This is a close-up image: 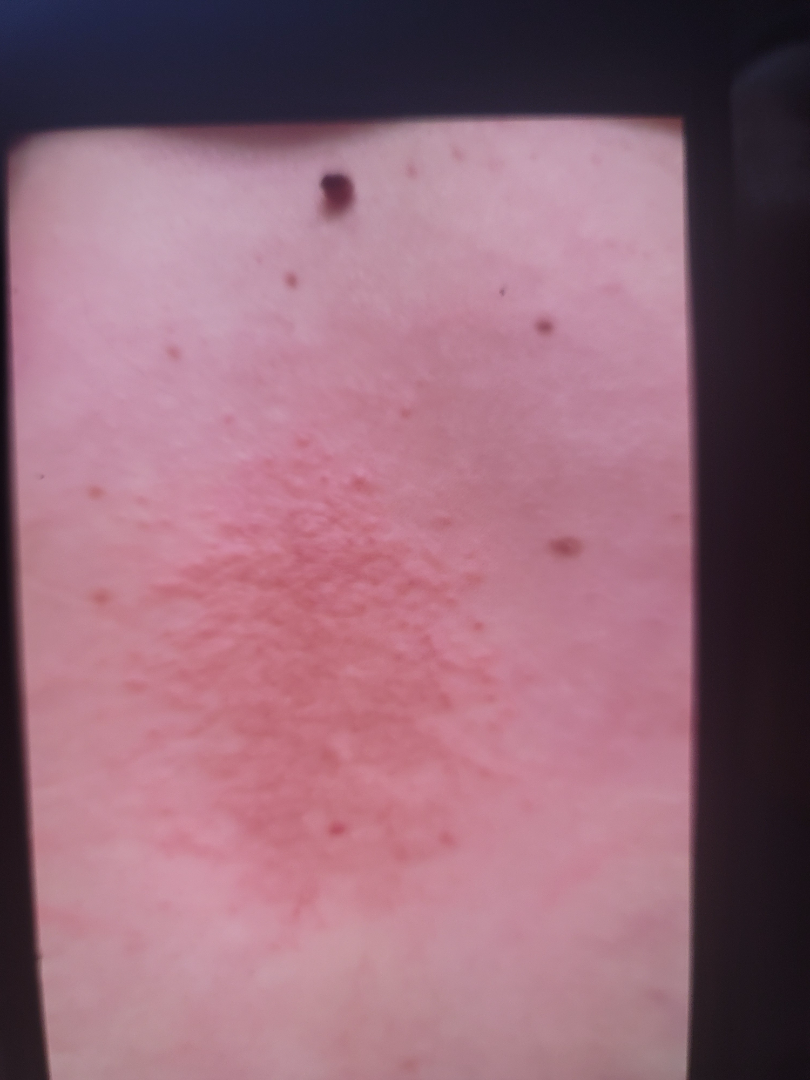The skin findings could not be characterized from the image.